The head or neck is involved · the photograph is a close-up of the affected area · the contributor is a female aged 50–59: 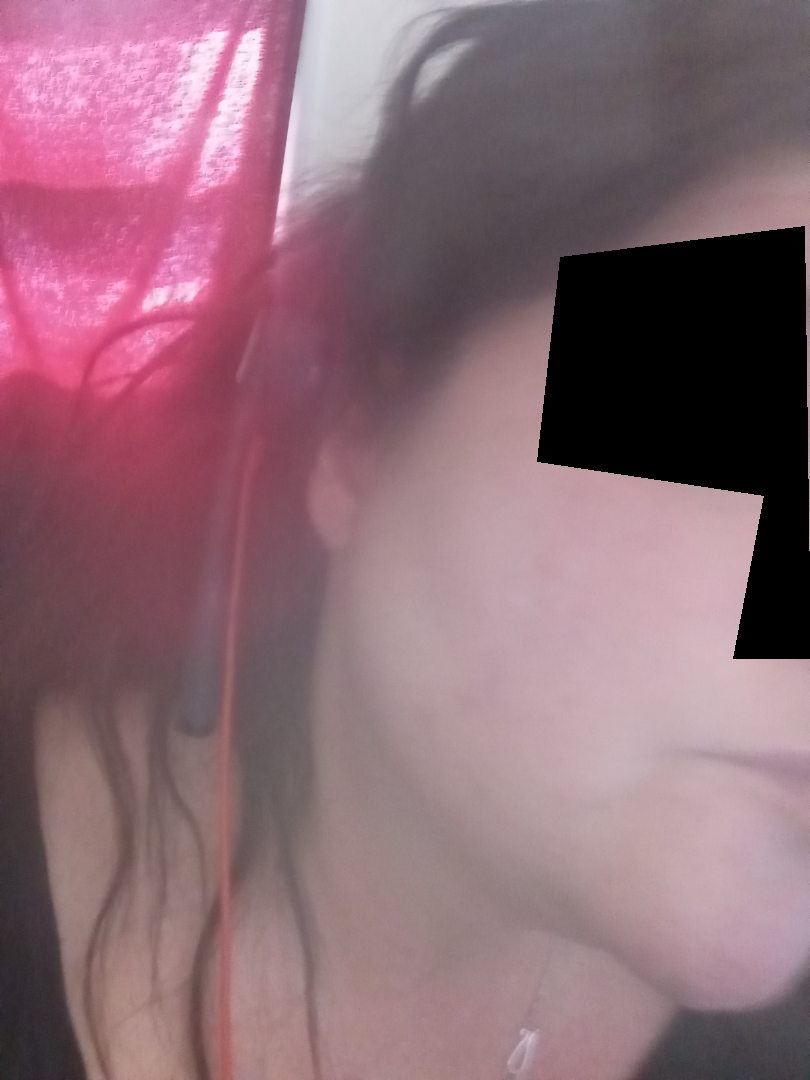Review:
The case was difficult to assess from the available photograph.